A female patient approximately 60 years of age, a dermoscopy image of a single skin lesion: 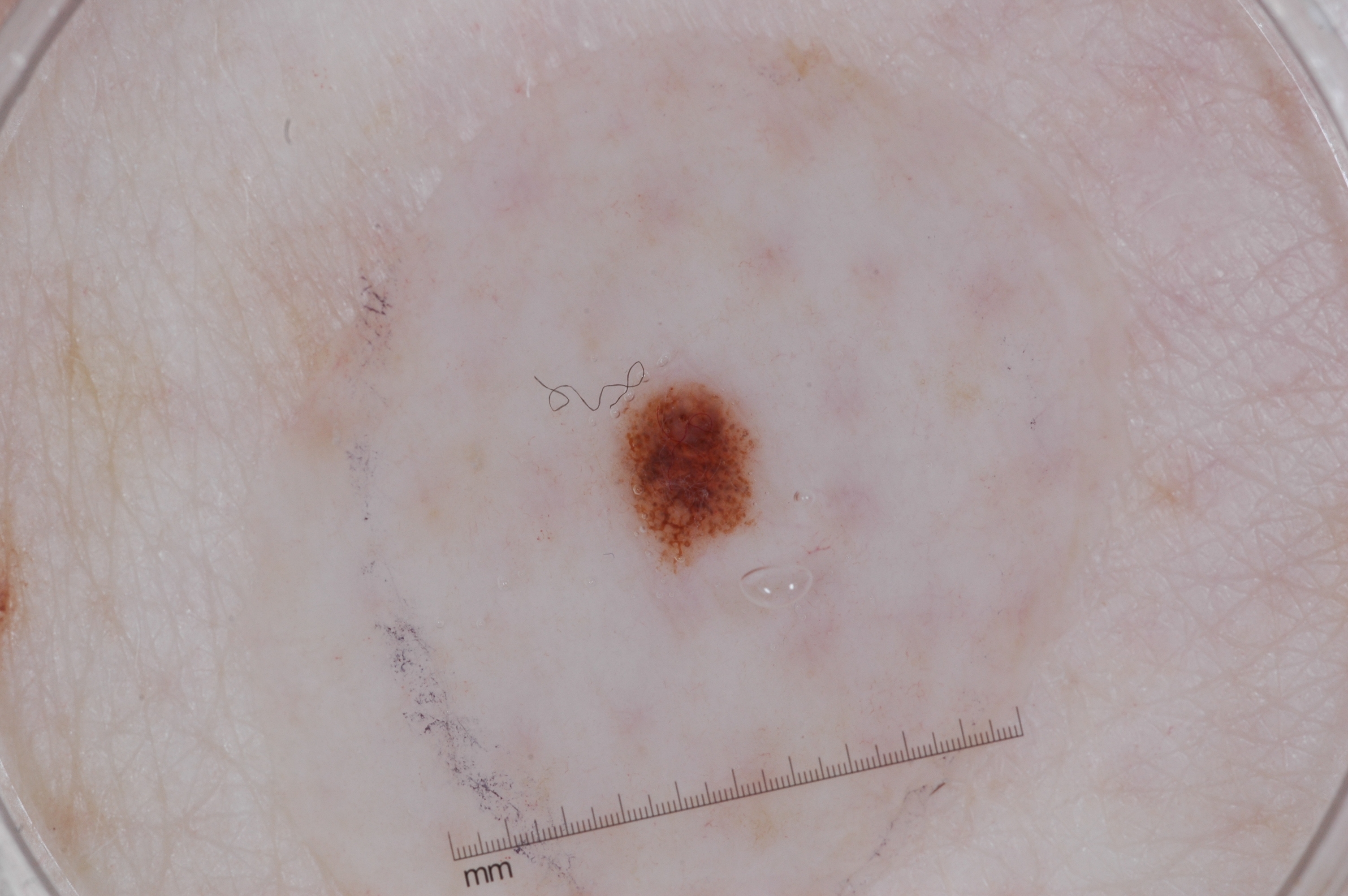bounding box — left=611, top=378, right=758, bottom=560 | dermoscopic features — pigment network; absent: streaks, milia-like cysts, and negative network | extent — ~2% of the field | diagnostic label — a melanocytic nevus, a benign lesion.